A male subject aged around 70.
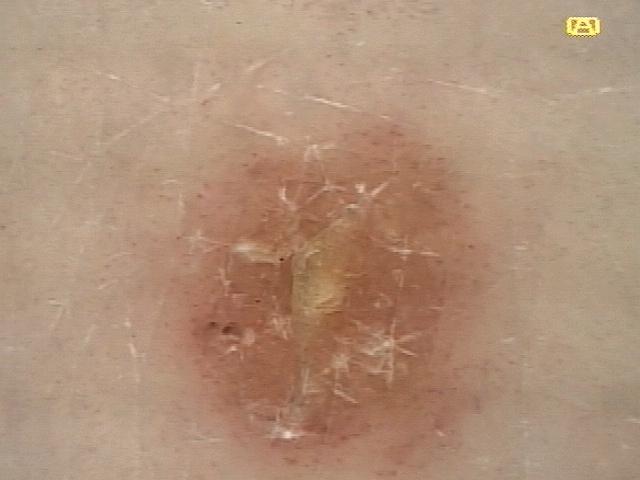Conclusion:
Clinically diagnosed as a solar or actinic keratosis.